The patient considered this a rash. The leg, head or neck, back of the torso, arm and front of the torso are involved. The lesion is described as rough or flaky. The condition has been present for more than one year. Skin tone: Fitzpatrick skin type IV. This image was taken at a distance. No constitutional symptoms were reported. The contributor is 50–59, female.
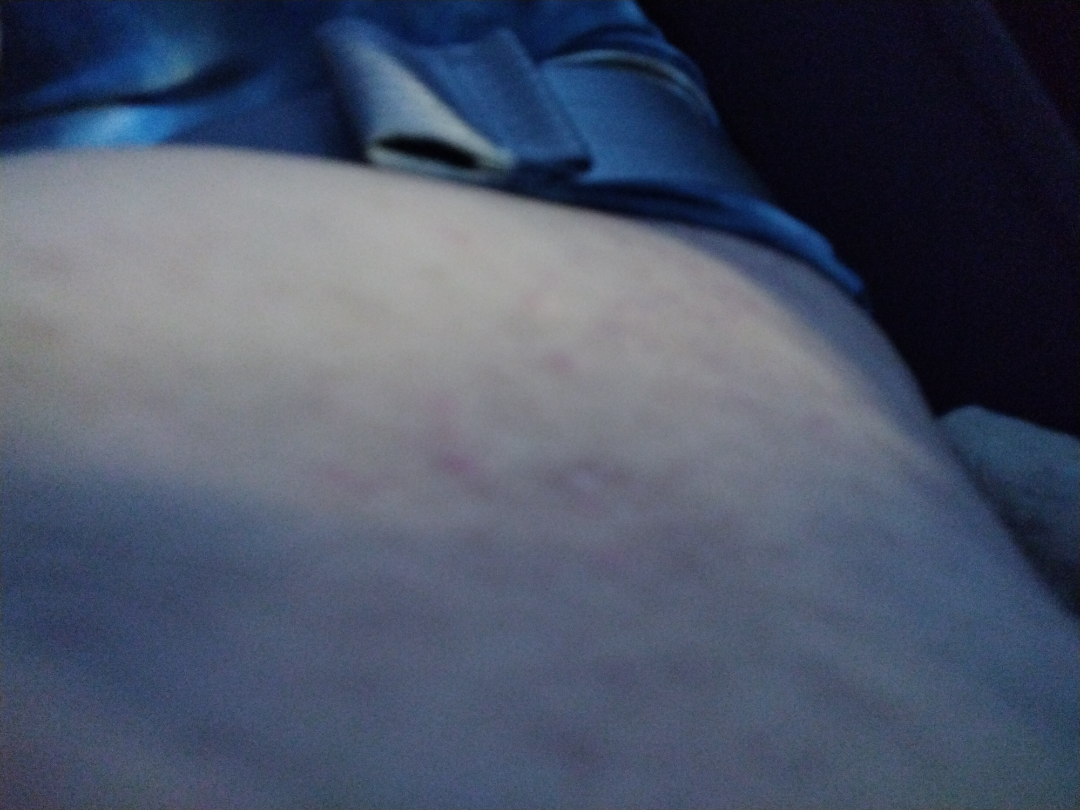On dermatologist assessment of the image: most likely Lichen Simplex Chronicus; also raised was Eczema.